A dermoscopy image of a single skin lesion:
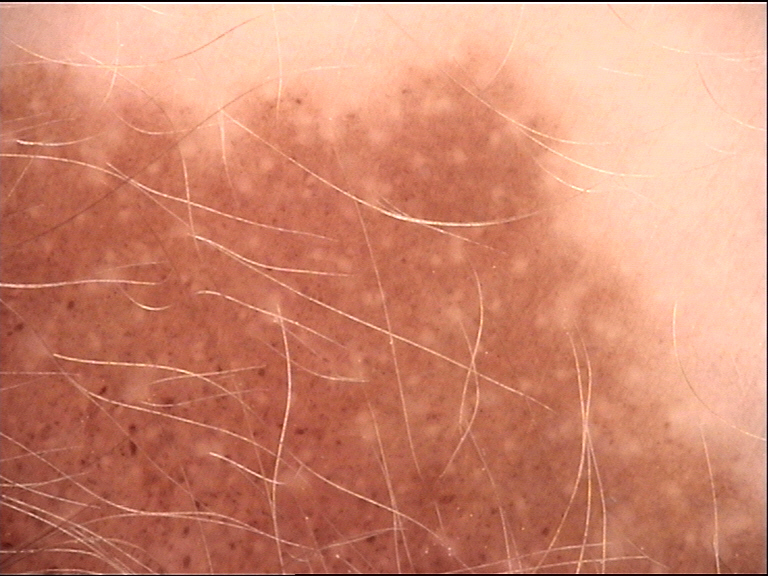| feature | finding |
|---|---|
| assessment | congenital junctional nevus (expert consensus) |